A close-up photograph; the patient is a female aged 18–29; the arm is involved:
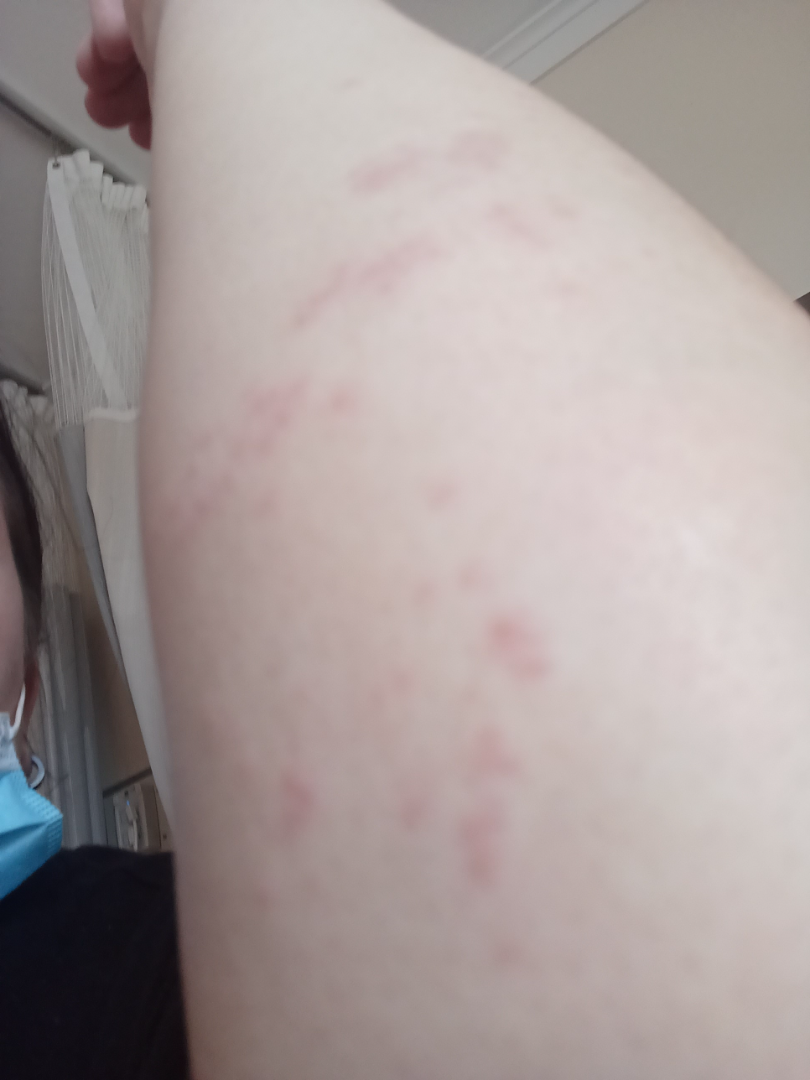Eczema (considered); Allergic Contact Dermatitis (considered).